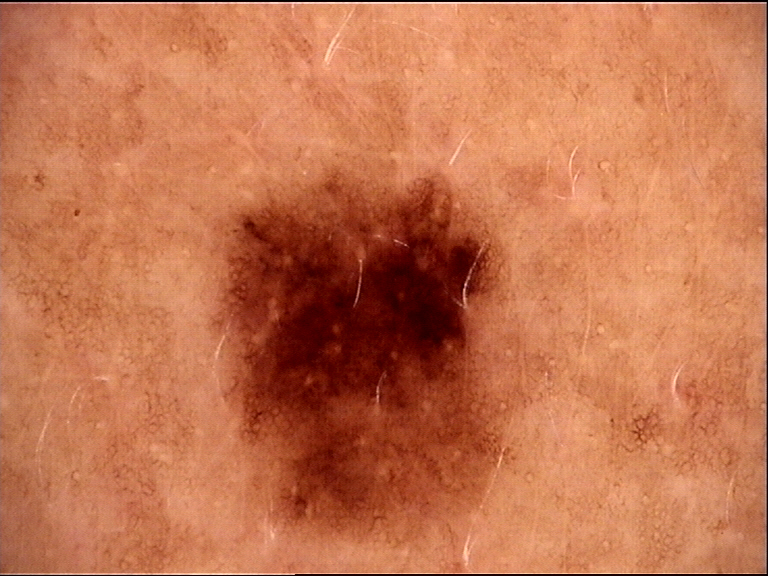Q: What was the diagnostic impression?
A: dysplastic junctional nevus (expert consensus)